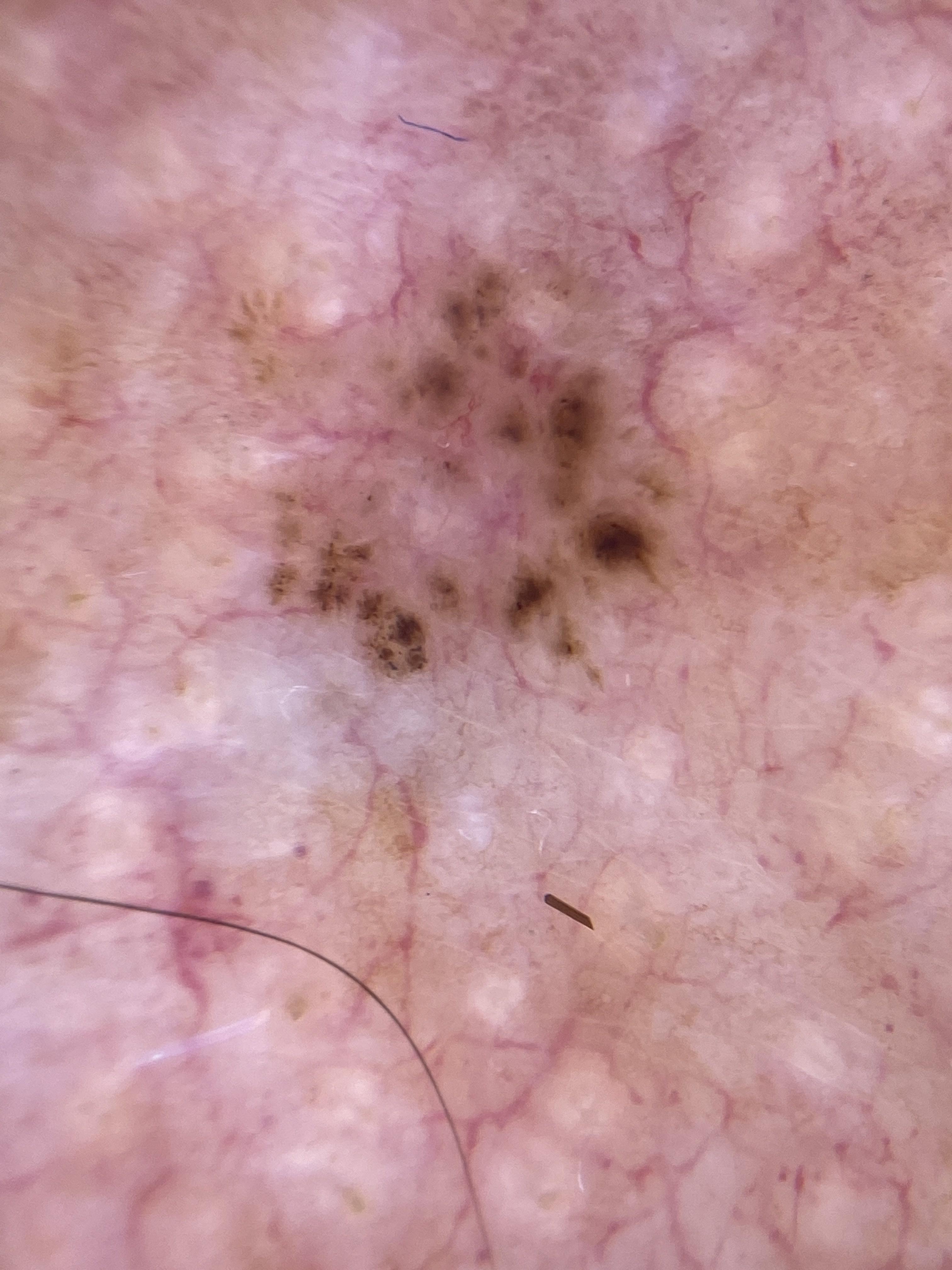image: dermoscopy
patient:
  age_approx: 70
  sex: male
diagnosis:
  name: Basal cell carcinoma
  malignancy: malignant
  confirmation: histopathology
  lineage: adnexal